A skin lesion imaged with a dermatoscope.
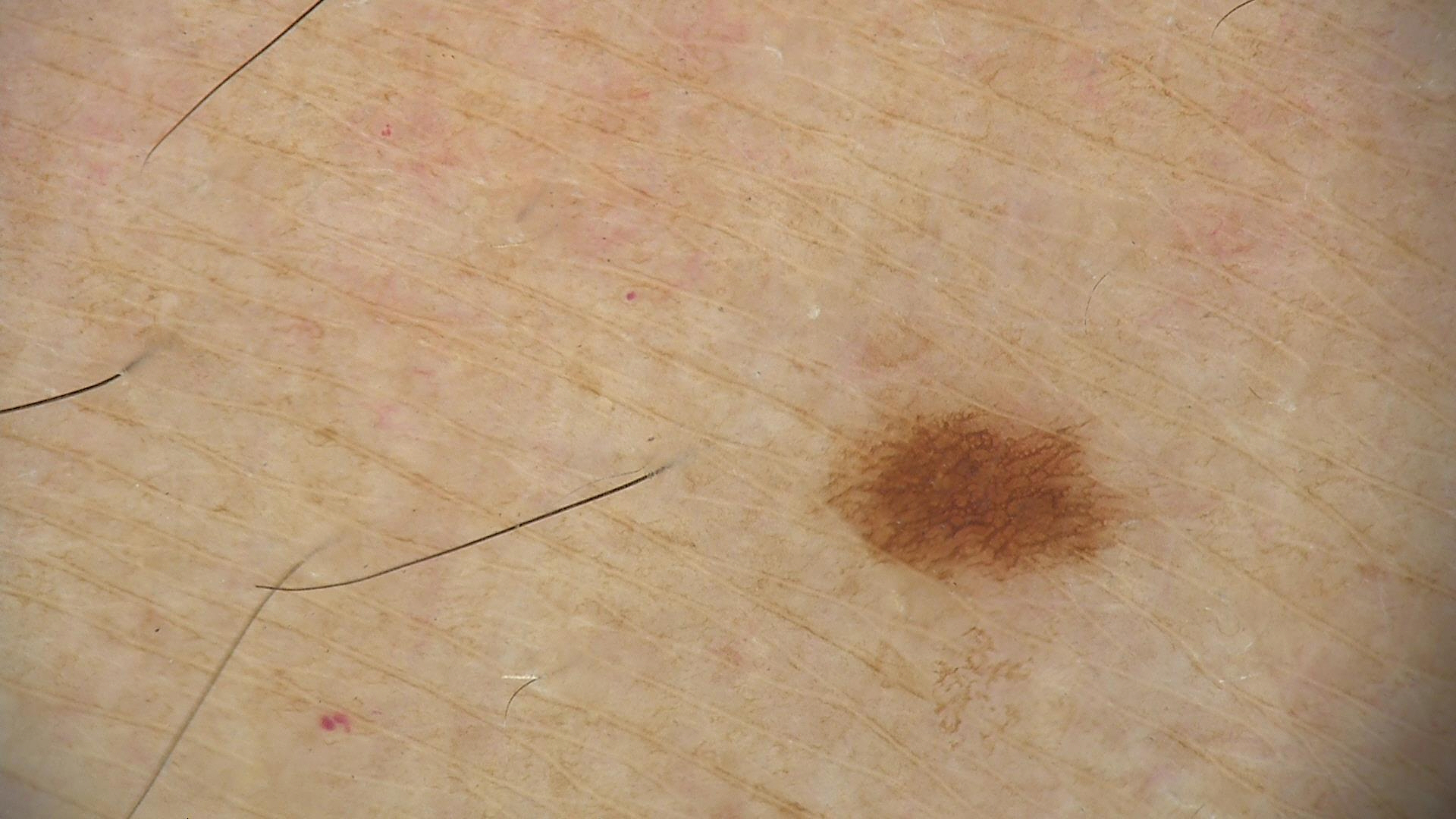diagnostic label: dysplastic junctional nevus (expert consensus).